A dermoscopic photograph of a skin lesion:
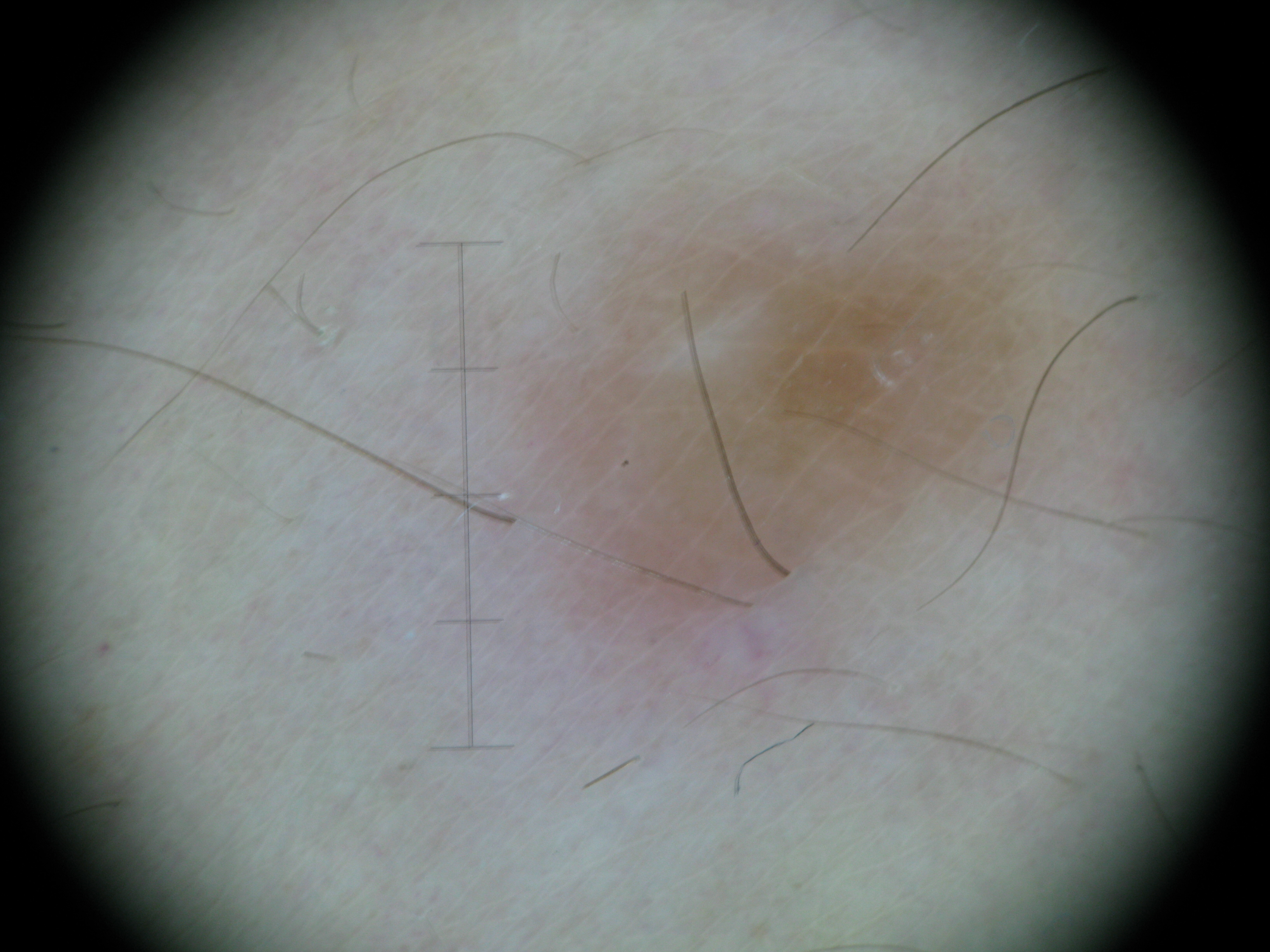The diagnosis was a fibro-histiocytic lesion — a dermatofibroma.